A skin lesion imaged with contact-polarized dermoscopy. A male subject in their mid-60s.
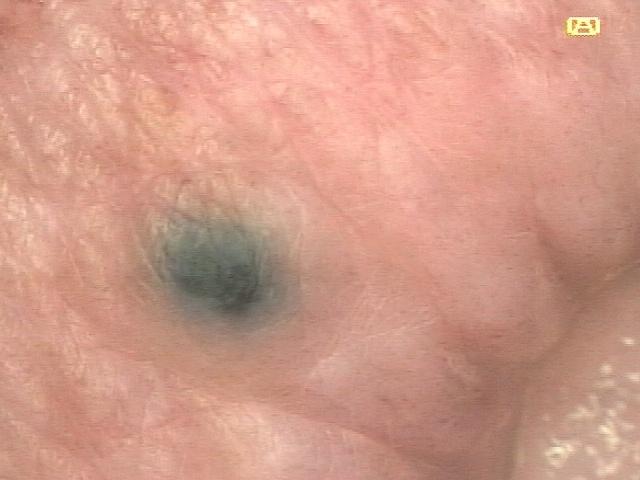The lesion involves the head or neck.
Consistent with a vascular lesion.